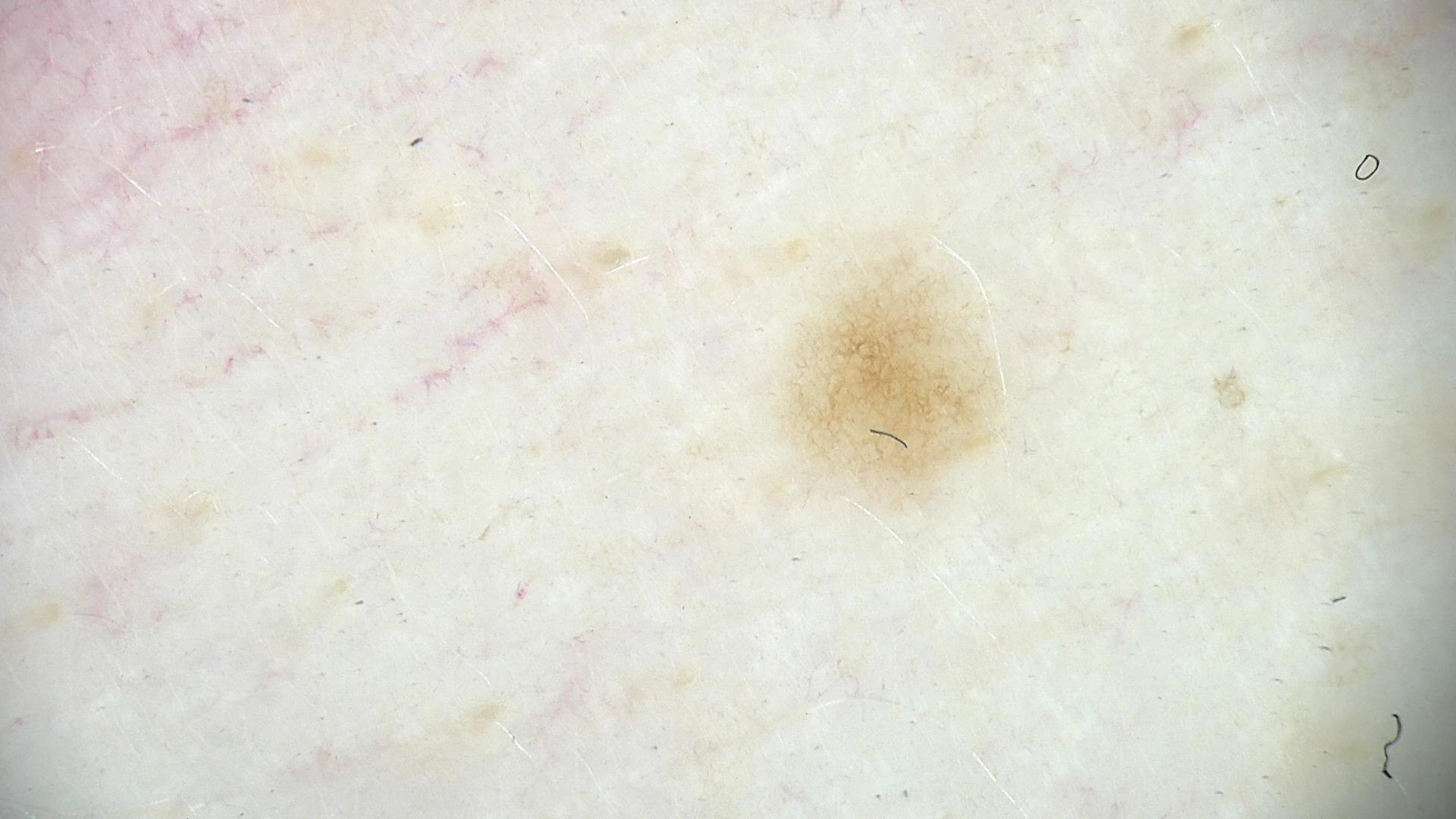Q: What was the diagnostic impression?
A: junctional nevus (expert consensus)